A patient 21 years old; a clinical photograph of a skin lesion.
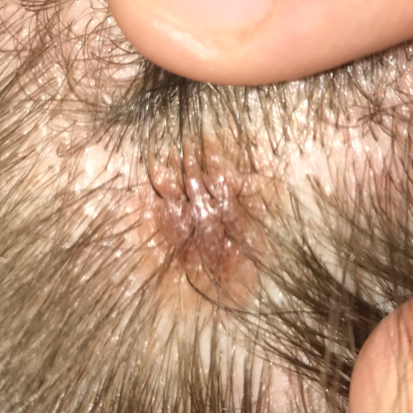Case summary:
The patient reports that the lesion is elevated and has grown.
Impression:
Expert review favored a benign lesion — a nevus.